This image was taken at an angle; the affected area is the leg and top or side of the foot.
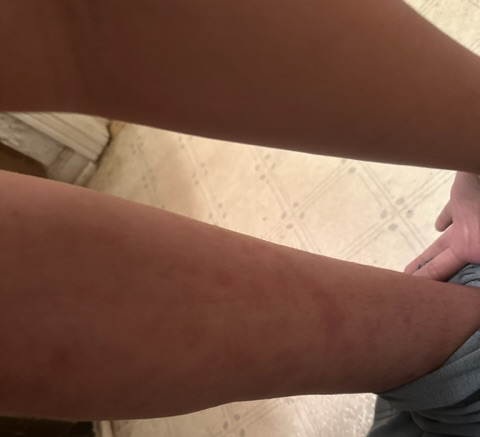Findings: The condition could not be reliably identified from the image. Background: Symptoms reported: darkening, bothersome appearance and enlargement. Reported duration is one to three months. Fitzpatrick phototype II; non-clinician graders estimated Monk skin tone scale 2–3. The patient reports associated fever. Self-categorized by the patient as a rash. The lesion is described as flat.